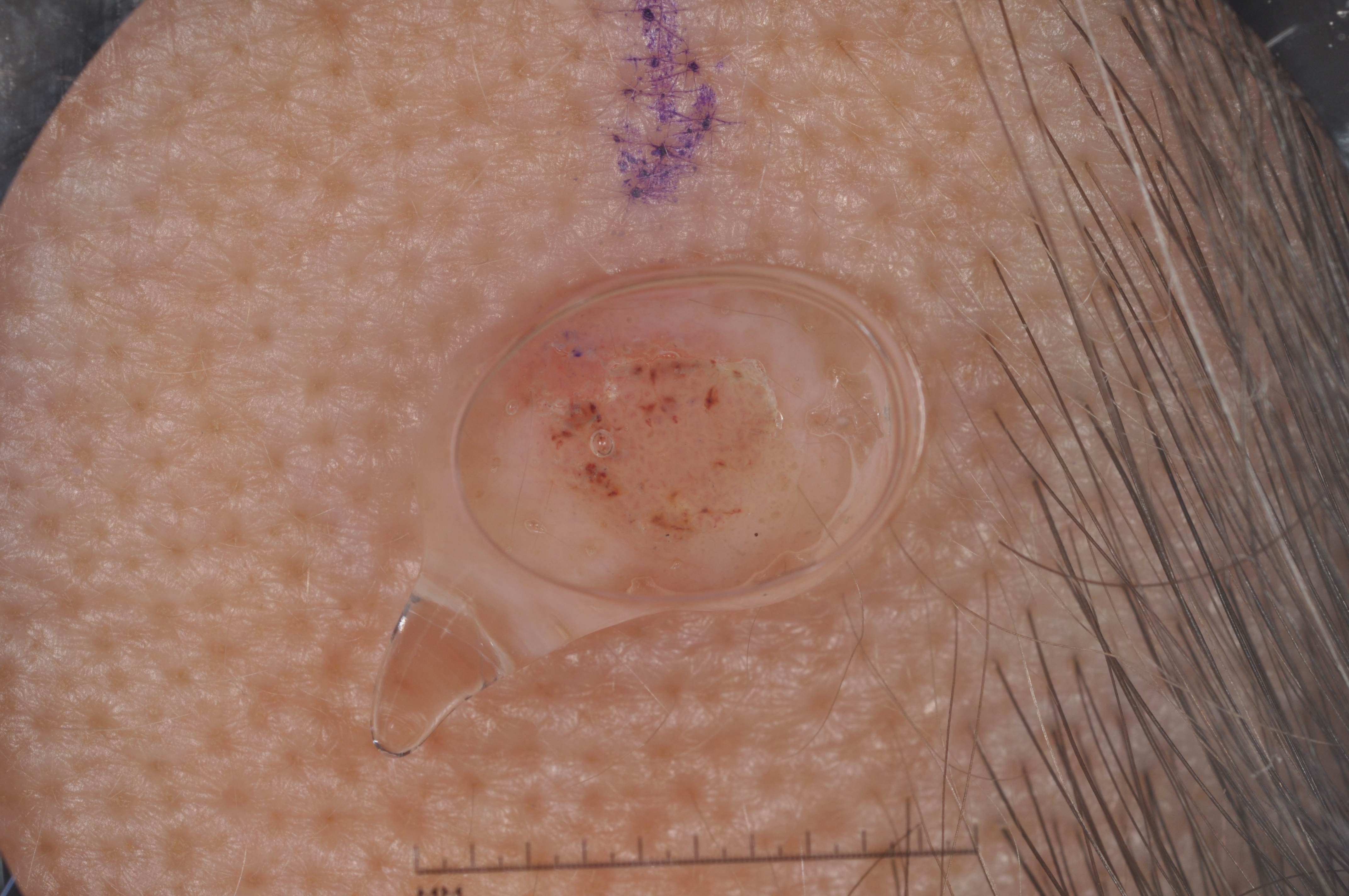Findings: Dermoscopy of a skin lesion. A female patient, aged 48 to 52. The lesion covers approximately 7% of the dermoscopic field. The visible lesion spans (422, 252, 769, 581). Dermoscopically, the lesion shows milia-like cysts; no negative network, streaks, or pigment network. Conclusion: Diagnosed as a seborrheic keratosis.